The lesion is described as rough or flaky, the affected area is the palm, the photograph is a close-up of the affected area, the condition has been present for three to twelve months — 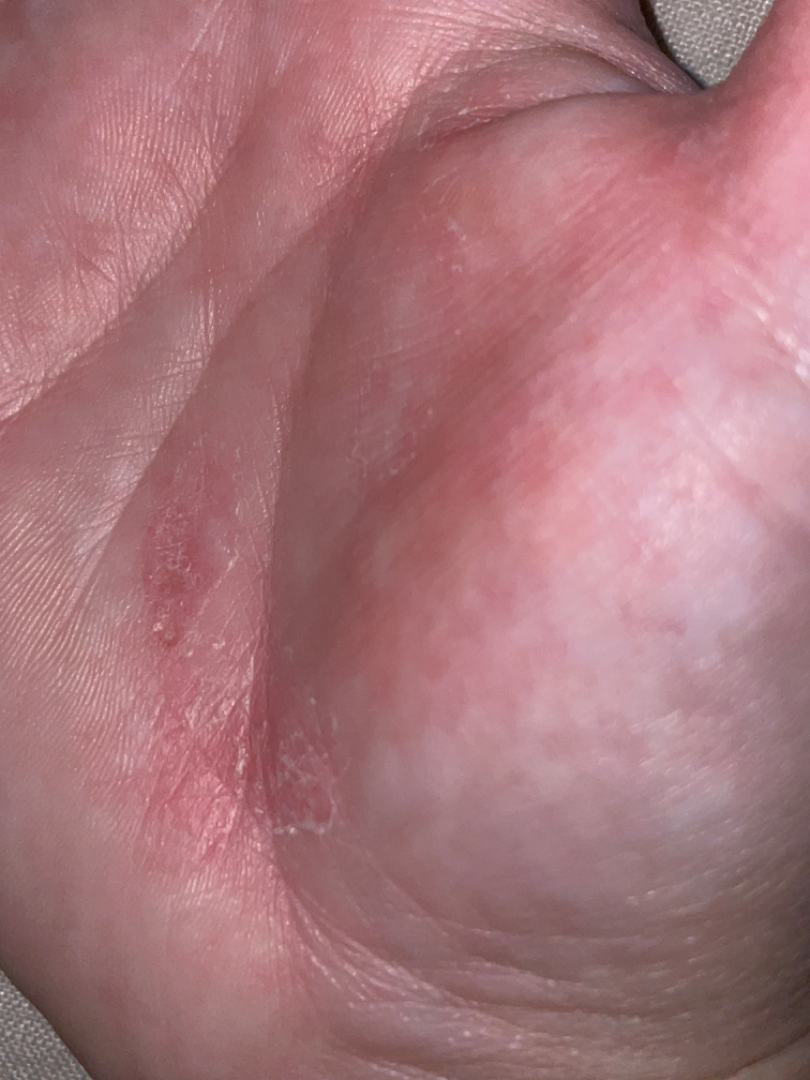Assessment:
On remote review of the image, Psoriasis, Eczema and Allergic Contact Dermatitis were considered with similar weight.